A dermoscopic photograph of a skin lesion. A male patient roughly 25 years of age — 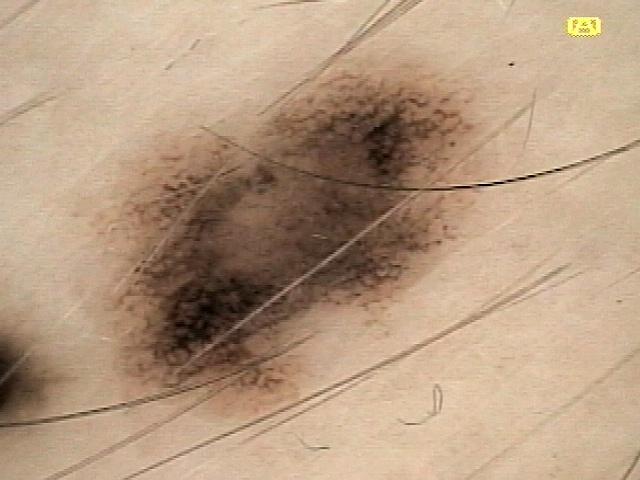Clinical context:
The lesion involves the trunk (the posterior trunk).
Conclusion:
On biopsy, the diagnosis was a melanoma.